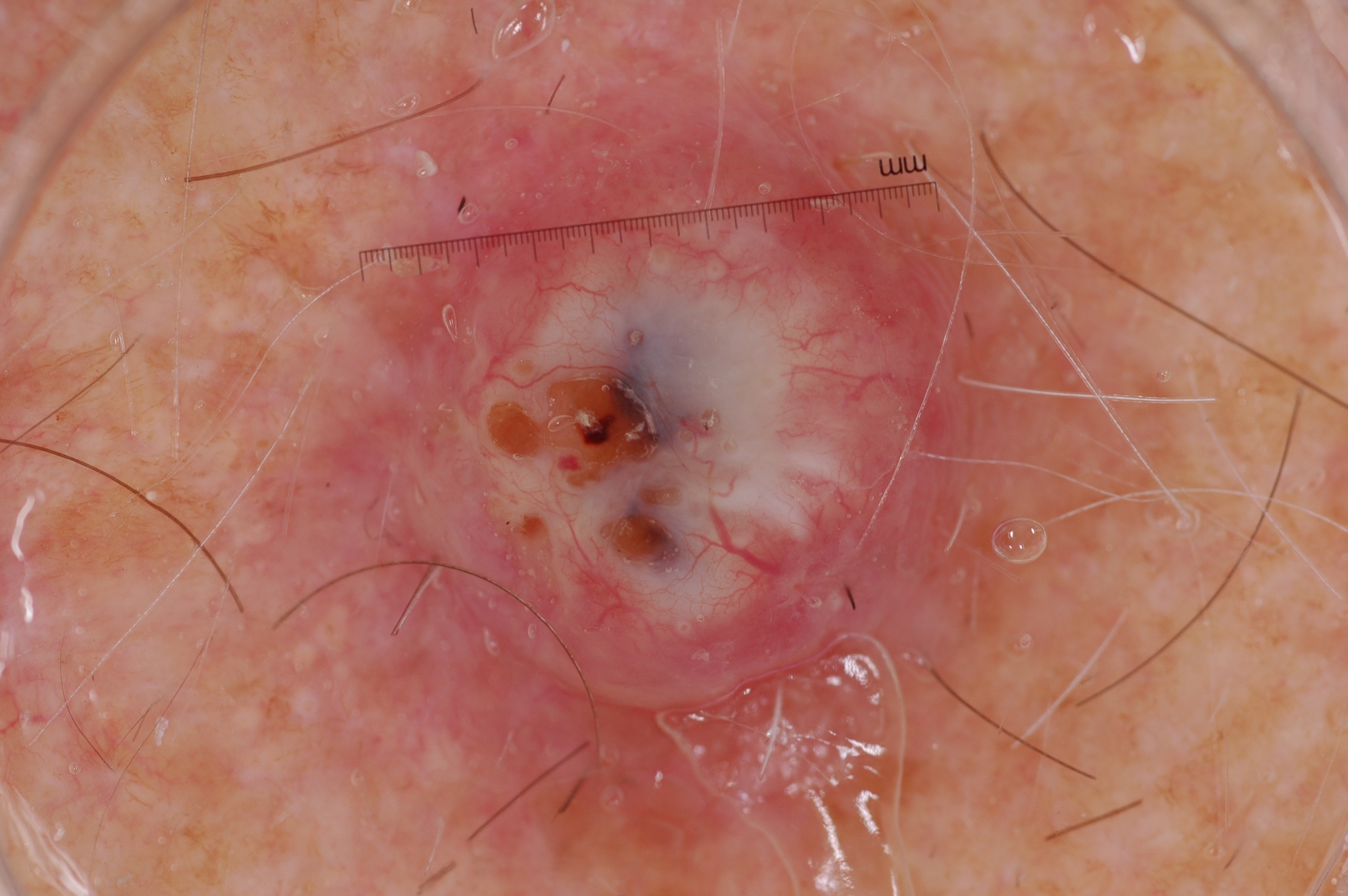A male subject aged around 70. A dermoscopic view of a skin lesion. The lesion occupies the region x1=237 y1=15 x2=1142 y2=860. Dermoscopic examination shows no streaks, milia-like cysts, pigment network, or negative network. Diagnosed as a seborrheic keratosis.